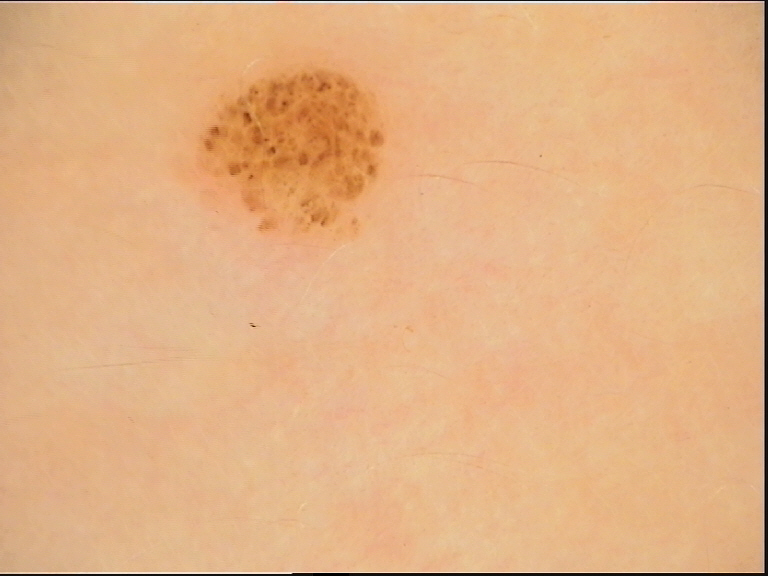modality=dermatoscopy | diagnosis=junctional nevus (expert consensus).